Skin type III; a female patient about 30 years old; the chart records no previous melanoma and no melanoma in first-degree relatives: 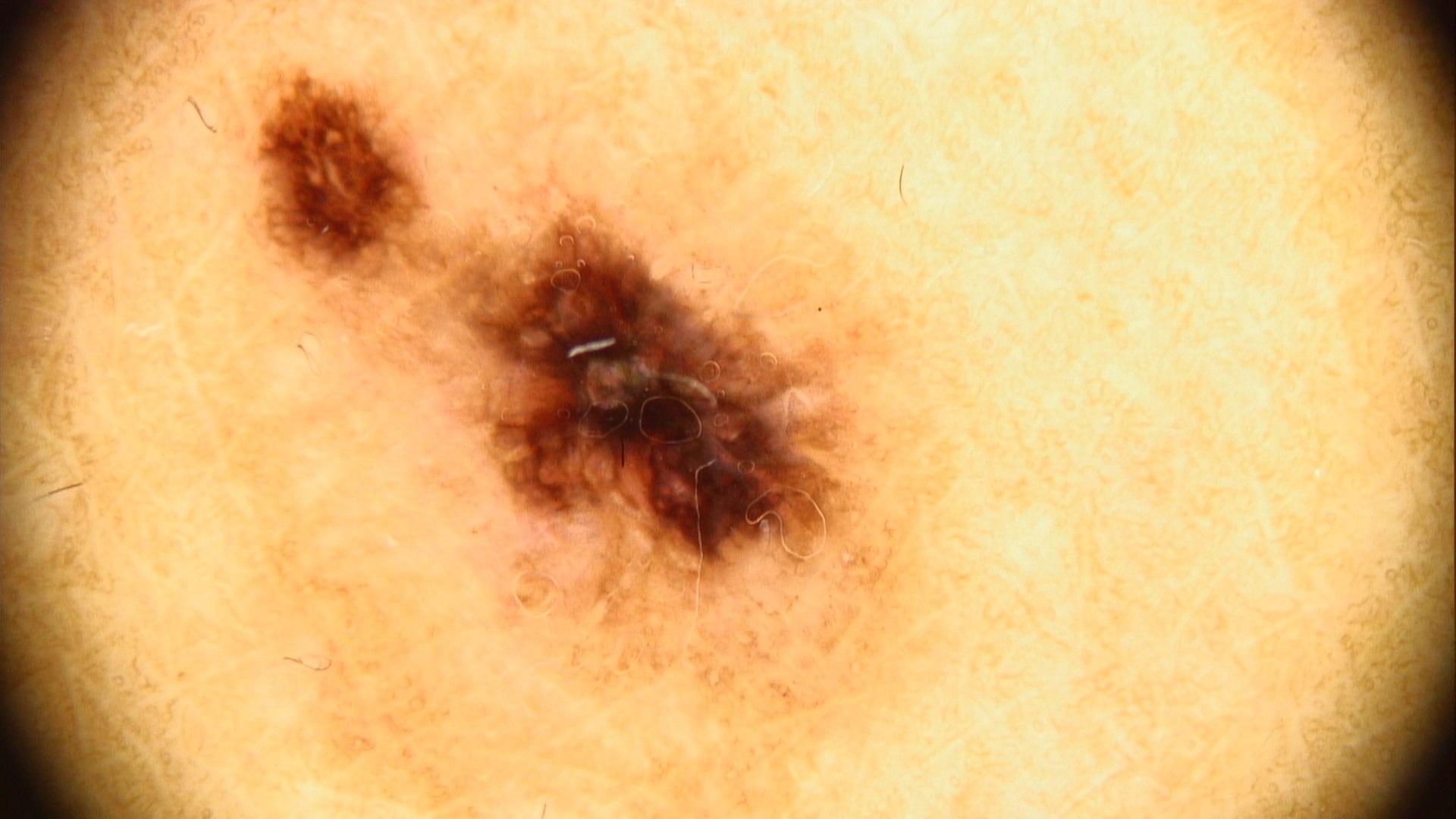Findings: The lesion involves a lower extremity. Pathology: On biopsy, the diagnosis was a skin cancer — a melanoma.